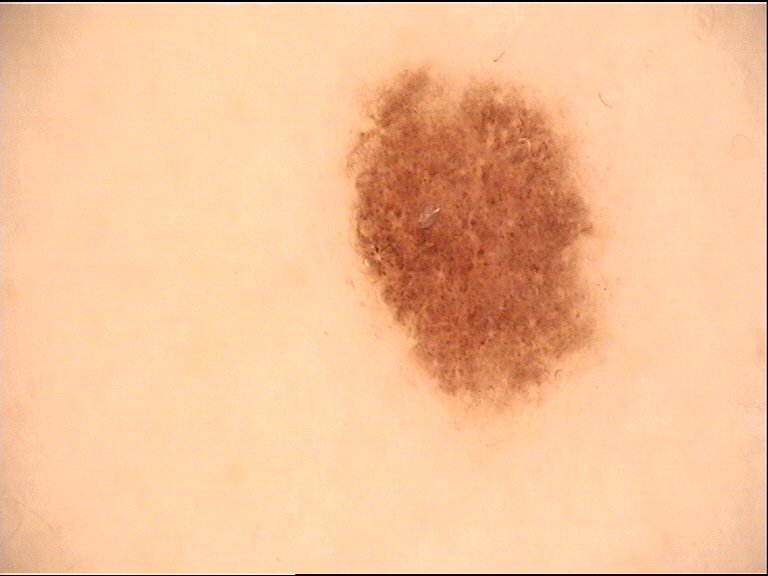Consistent with a dysplastic junctional nevus.